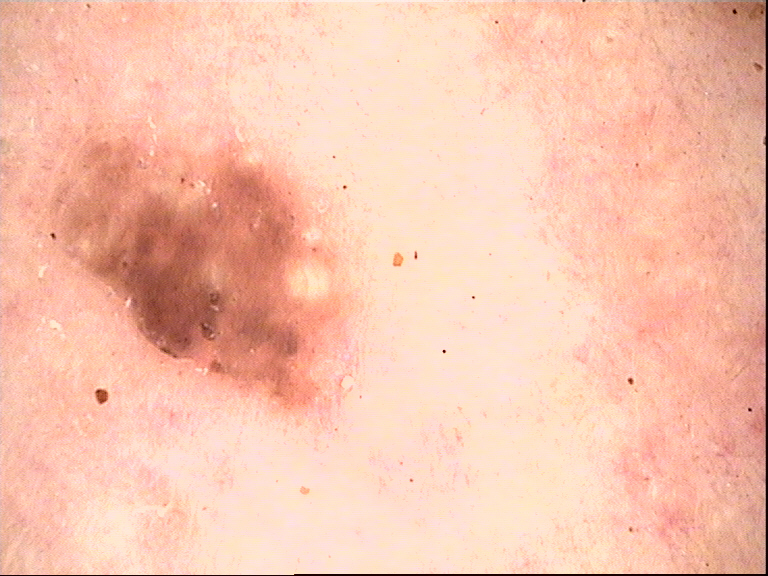Diagnosed as a seborrheic keratosis.